A dermoscopic close-up of a skin lesion:
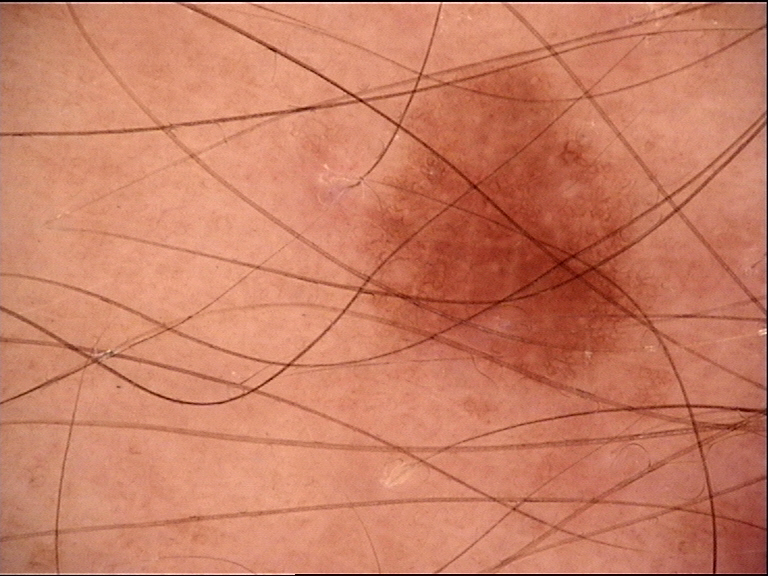class — dysplastic junctional nevus (expert consensus).